A dermoscopic close-up of a skin lesion: 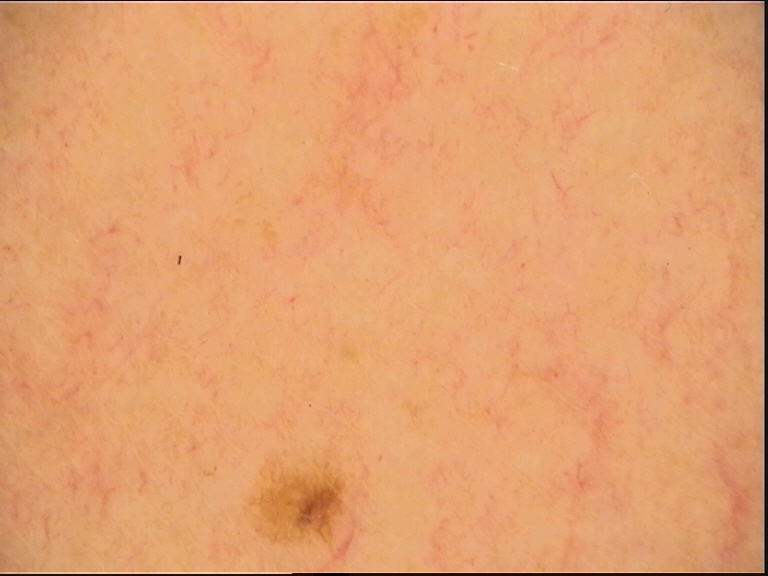The diagnostic label was a benign lesion — a dysplastic junctional nevus.